The lesion is associated with enlargement and itching · the patient is a female aged 18–29 · the arm is involved · the patient reports the lesion is raised or bumpy · Fitzpatrick phototype III · a close-up photograph · present for about one day · the patient considered this a rash · no relevant systemic symptoms — 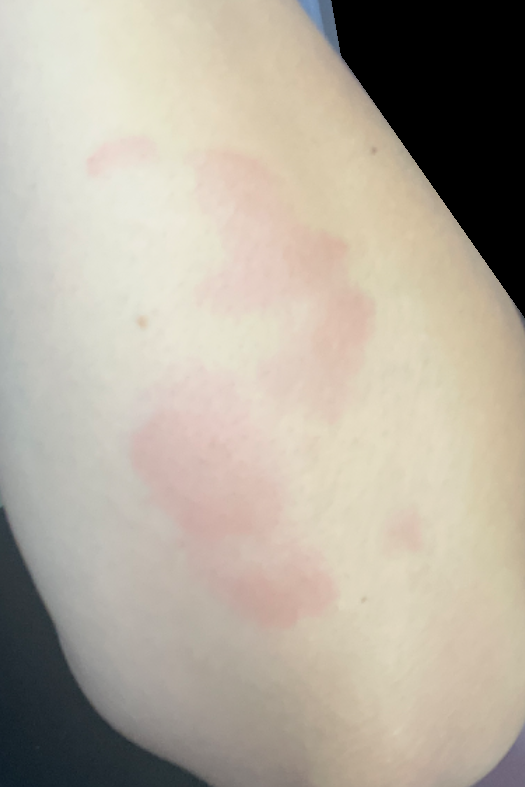Review:
The image was not sufficient for the reviewer to characterize the skin condition.